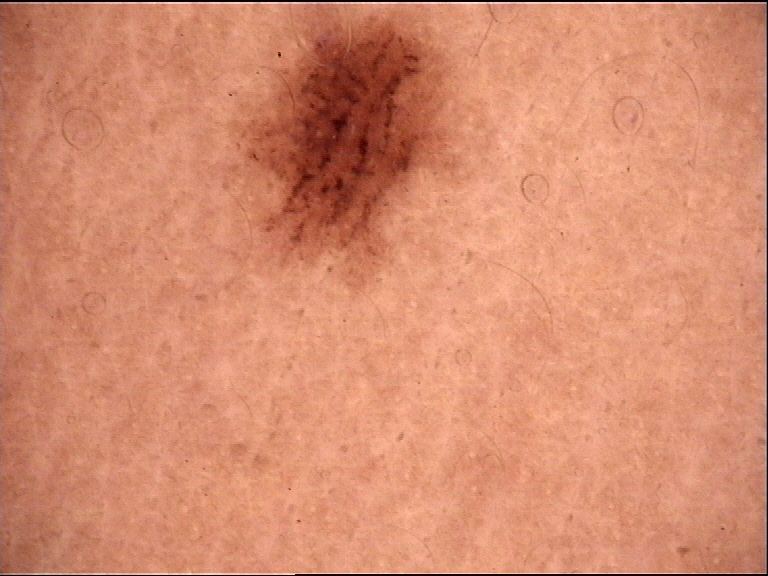Case: A dermoscopic image of a skin lesion. Conclusion: Classified as a benign lesion — a dysplastic junctional nevus.